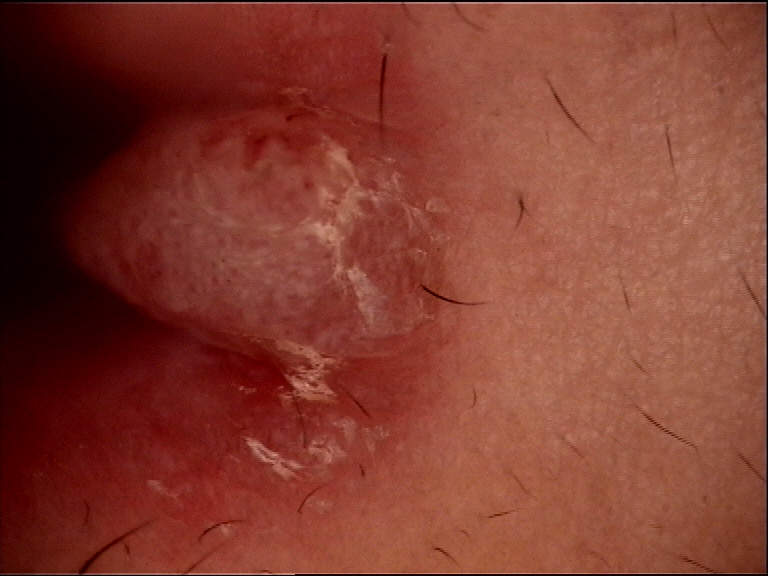imaging=dermatoscopy
category=keratinocytic
diagnosis=squamous cell carcinoma (biopsy-proven)